The photograph is a close-up of the affected area · located on the leg · the subject is 50–59, male:
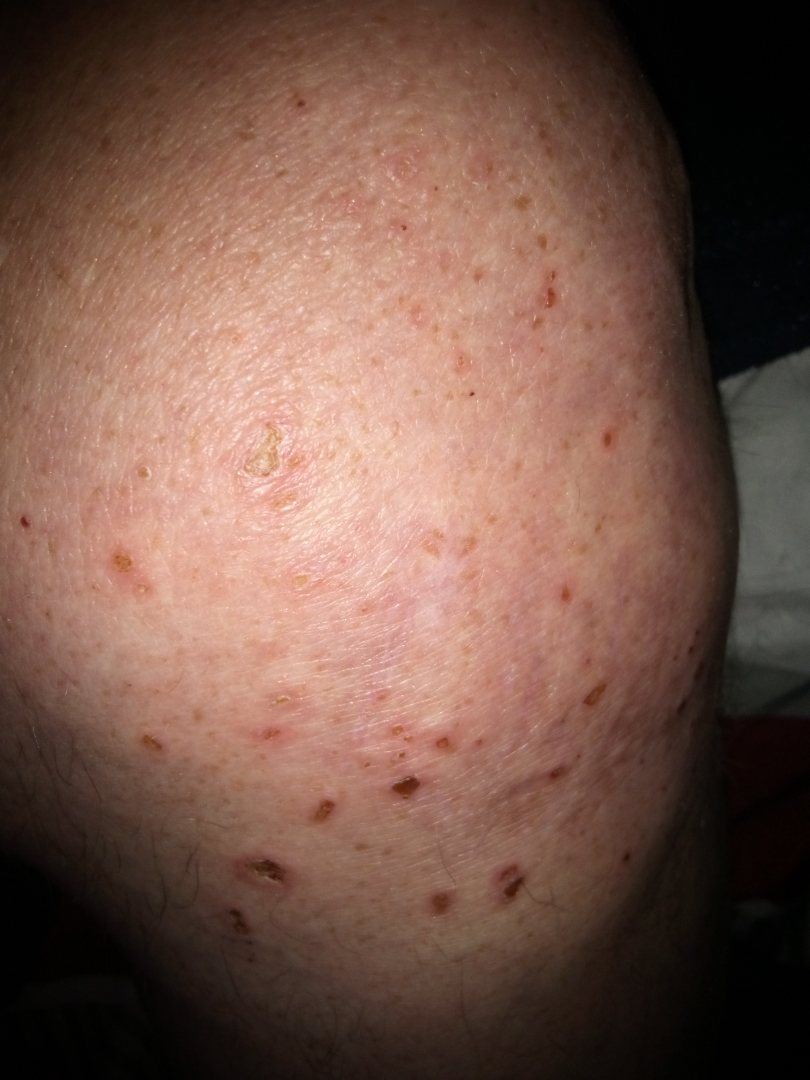{"assessment": "unable to determine"}